The front of the torso, arm and back of the hand are involved. The photograph was taken at a distance. The subject is a female aged 50–59: 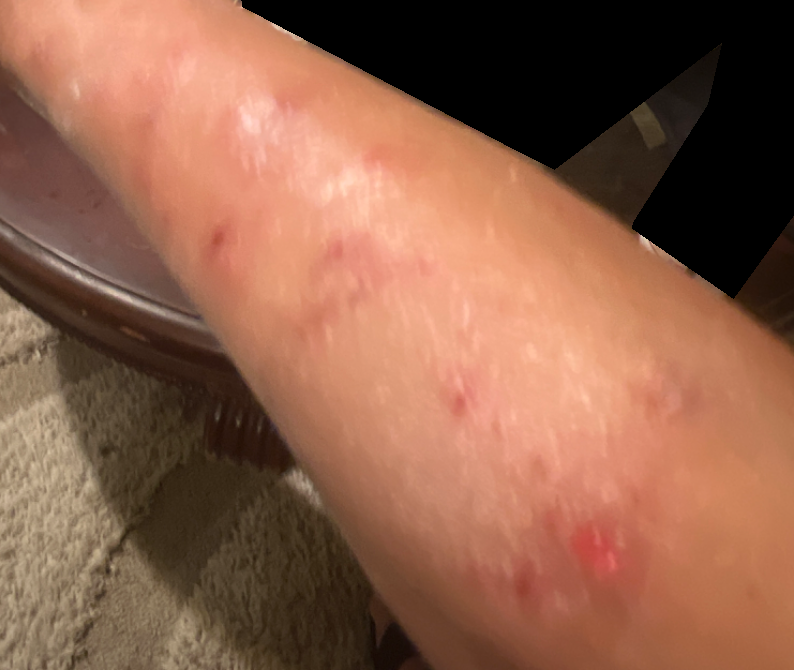Clinical context:
The contributor reports associated fatigue. Skin tone: human graders estimated MST 4 (US pool) or 3 (India pool). The lesion is described as raised or bumpy. Reported duration is one to four weeks. The patient described the issue as a growth or mole.
Assessment:
On photographic review, the differential, in no particular order, includes Prurigo nodularis and Abrasion, scrape, or scab; a more distant consideration is Insect Bite; less probable is Allergic Contact Dermatitis.